The lesion is associated with itching, burning, pain, bothersome appearance and darkening; texture is reported as raised or bumpy; present for less than one week; located on the arm; Fitzpatrick phototype IV; the photo was captured at an angle; no constitutional symptoms were reported.
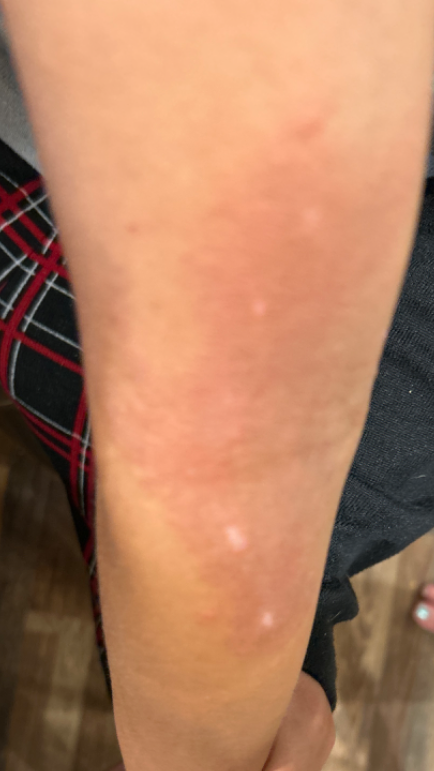clinical impression — Eczema (weight 1.00).